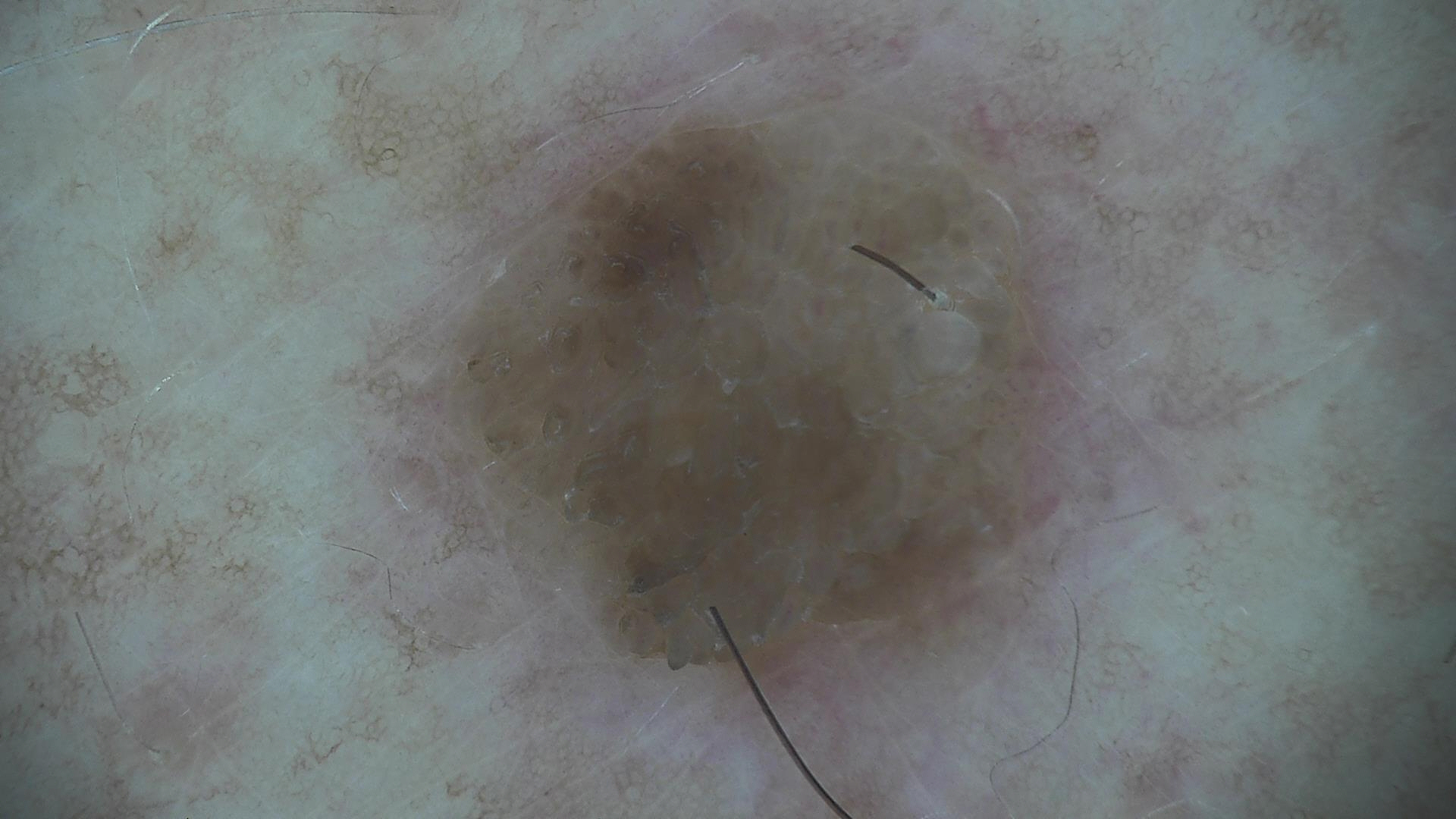{"diagnosis": {"name": "seborrheic keratosis", "code": "sk", "malignancy": "benign", "super_class": "non-melanocytic", "confirmation": "expert consensus"}}